The condition has been present for more than one year. The patient considered this a rash. The lesion involves the arm. An image taken at an angle. Texture is reported as raised or bumpy: 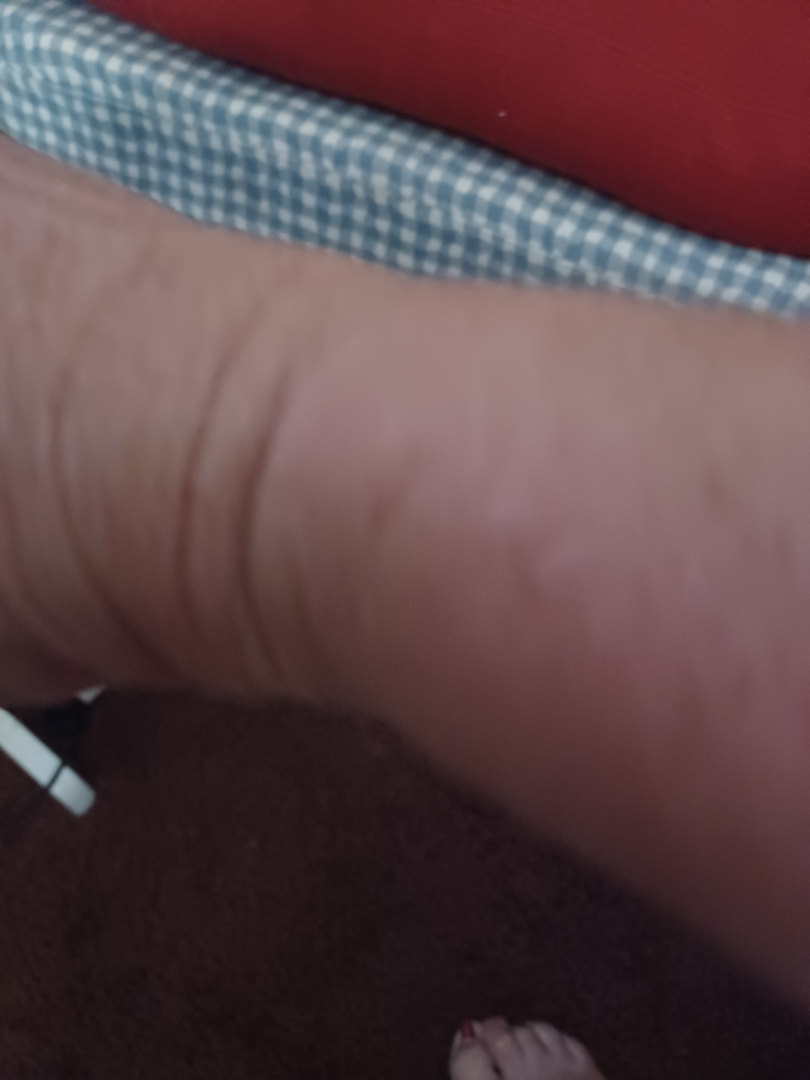{
  "assessment": "ungradable on photographic review"
}